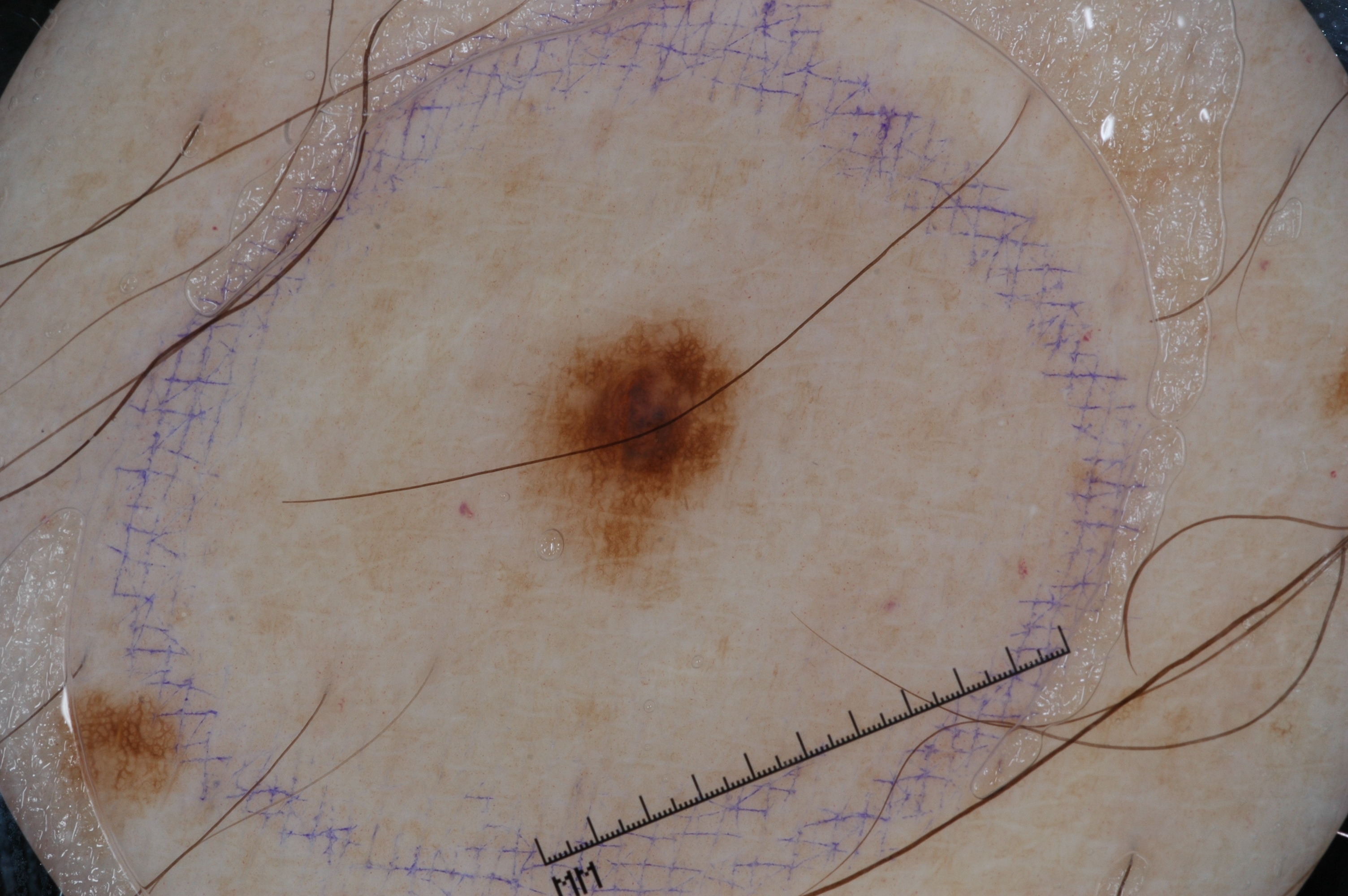imaging: dermoscopy of a skin lesion; patient: male, aged around 50; dermoscopic features: pigment network; size: small; location: 527 315 737 567; diagnosis: a melanocytic nevus, a benign lesion.